A dermoscopy image of a single skin lesion: 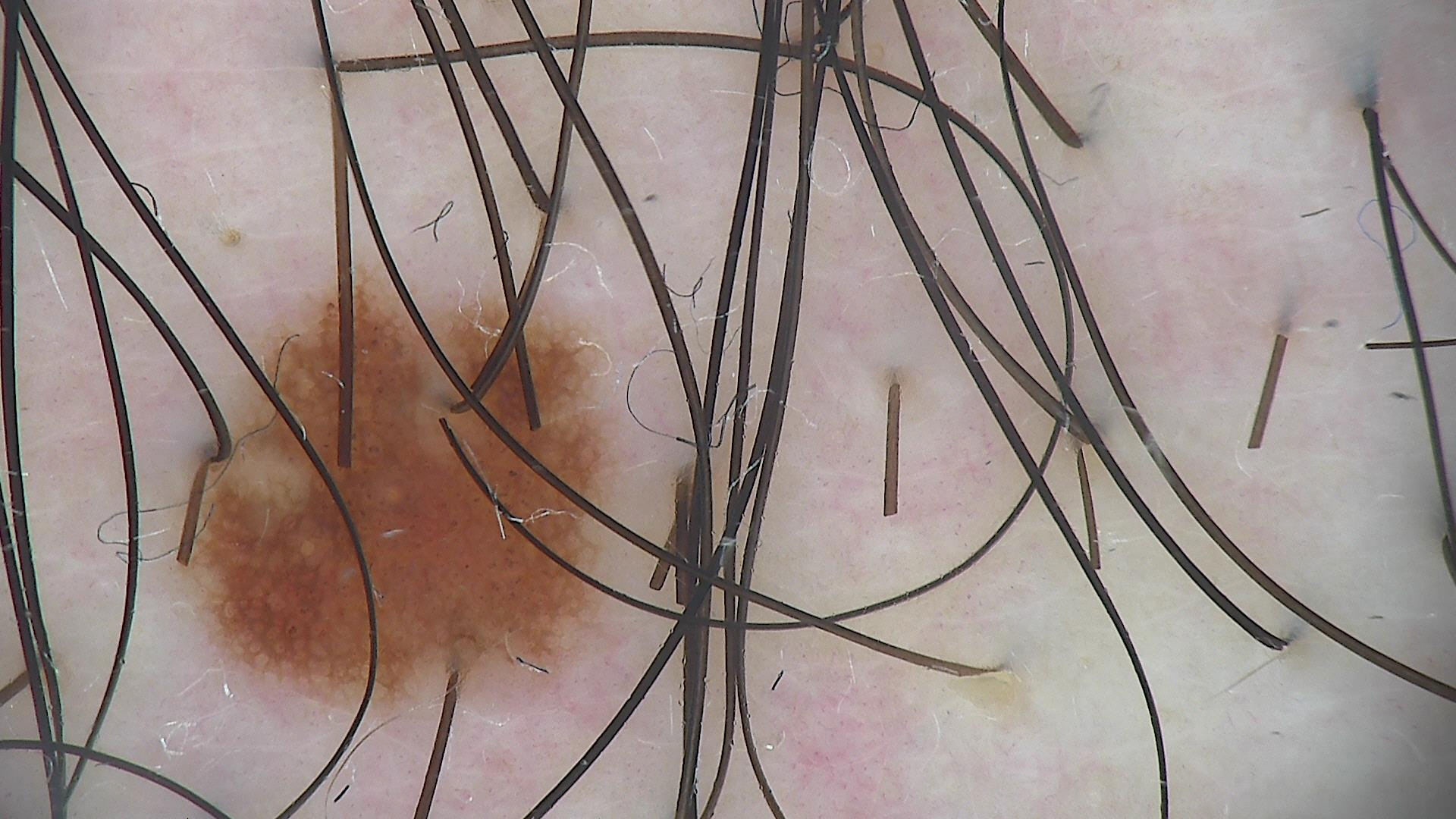<dermoscopy>
<diagnosis>
<name>dysplastic junctional nevus</name>
<code>jd</code>
<malignancy>benign</malignancy>
<super_class>melanocytic</super_class>
<confirmation>expert consensus</confirmation>
</diagnosis>
</dermoscopy>